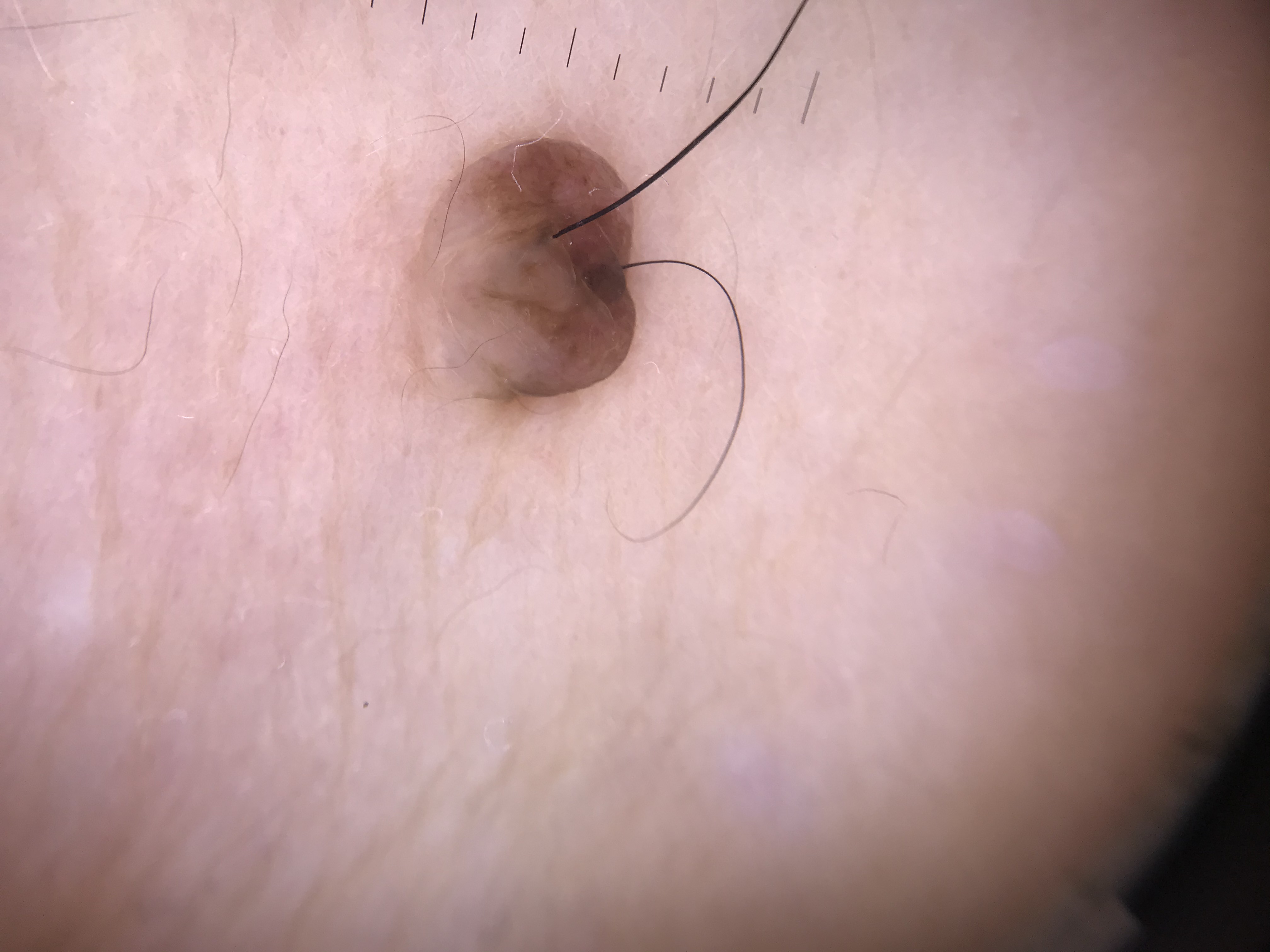A dermoscopy image of a single skin lesion. The diagnosis was a banal lesion — a dermal nevus.